A dermoscopic close-up of a skin lesion.
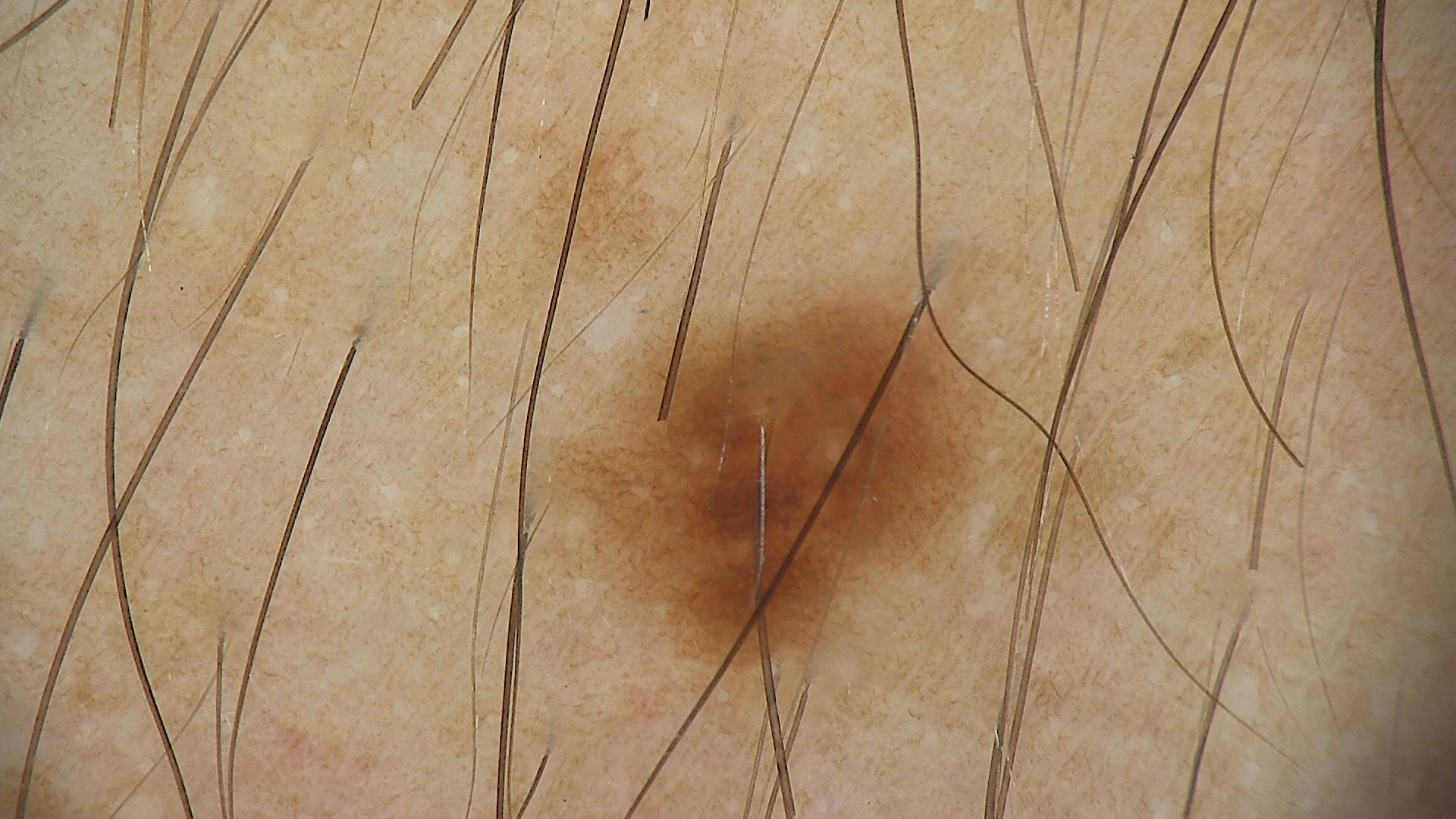Diagnosed as a dysplastic junctional nevus.